The affected area is the arm; the patient indicates the condition has been present for about one day; this image was taken at a distance; symptoms reported: burning; the patient described the issue as a rash; Fitzpatrick phototype I; the patient indicates the lesion is rough or flaky: 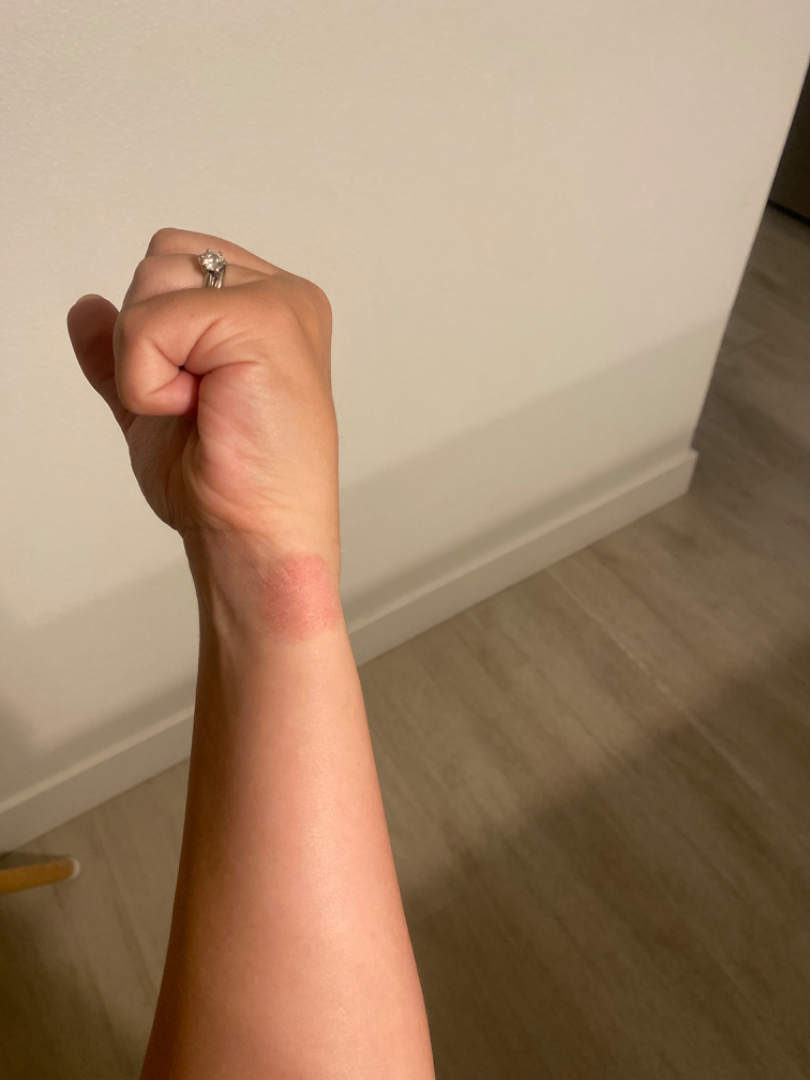Impression: A single dermatologist reviewed the case: the leading impression is Eczema; with consideration of Psoriasis; less probable is Tinea.